The back of the torso is involved. The contributor is a male aged 18–29. This is a close-up image.
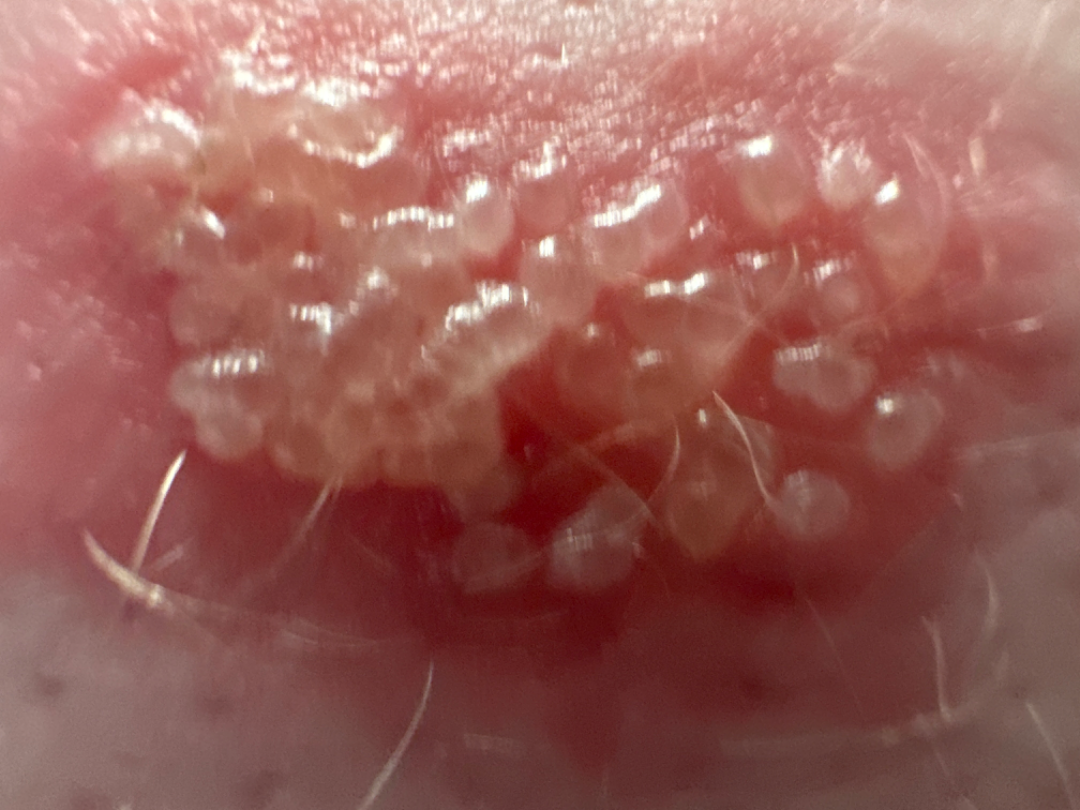The contributor reports pain. Self-categorized by the patient as a rash. Texture is reported as raised or bumpy. FST I; lay graders estimated Monk skin tone scale 1 or 2 (two reviewer pools). On dermatologist assessment of the image, most likely Herpes Simplex; less probable is Lymphangioma; lower on the differential is Herpes Zoster.